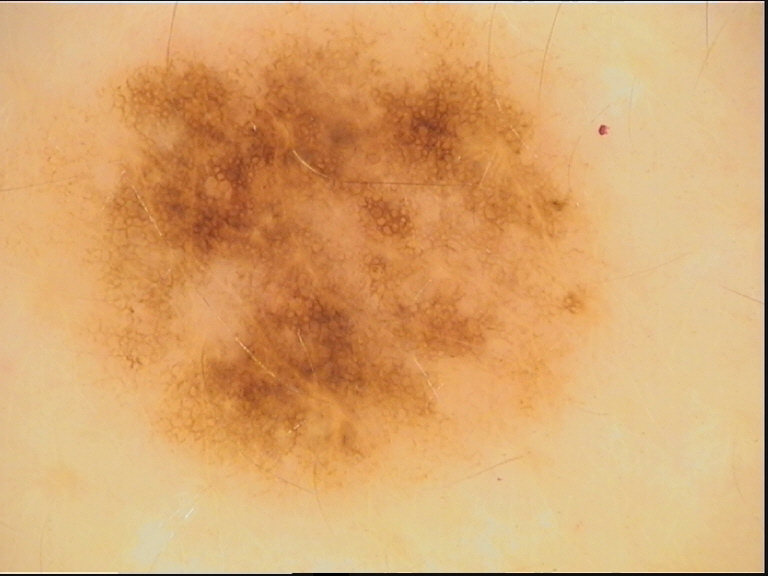diagnosis = dysplastic junctional nevus (expert consensus).